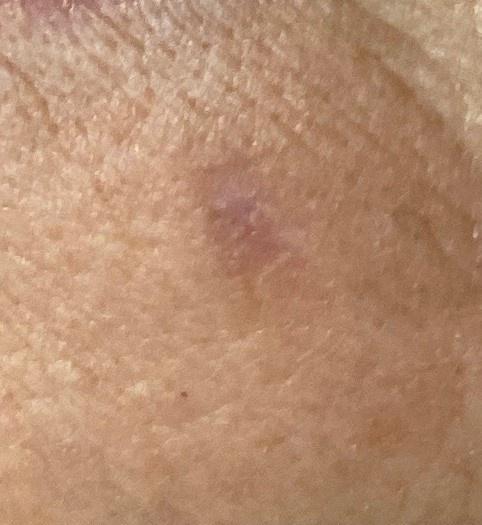A clinical photograph of a skin lesion.
Located on the head or neck.
Biopsy-confirmed as a malignant lesion — a squamous cell carcinoma.